A dermoscopy image of a single skin lesion.
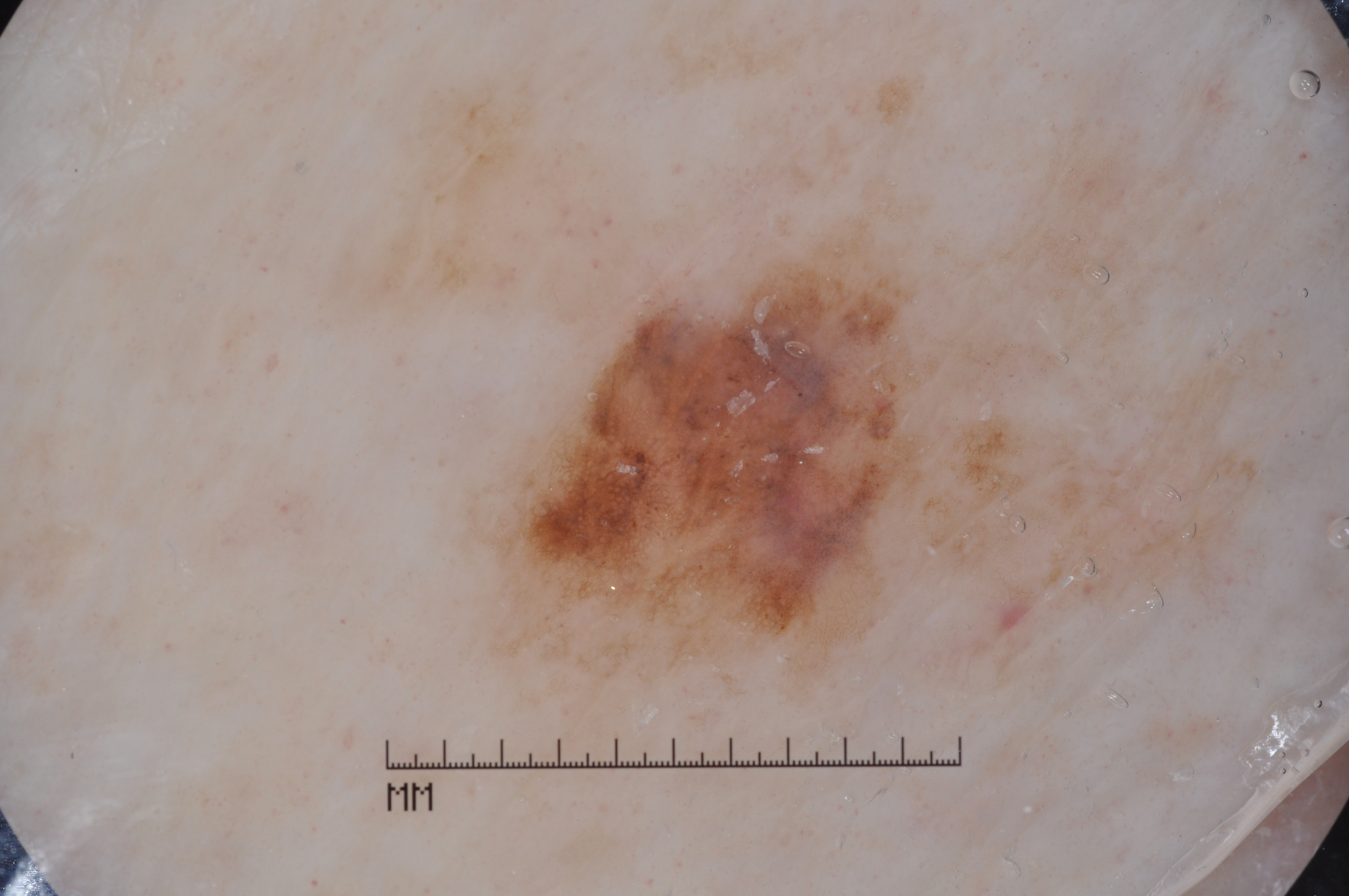Image and clinical context: With coordinates (x1, y1, x2, y2), lesion location: 456 249 964 711. Dermoscopy demonstrates pigment network and milia-like cysts. Diagnosis: Histopathologically confirmed as a melanoma.